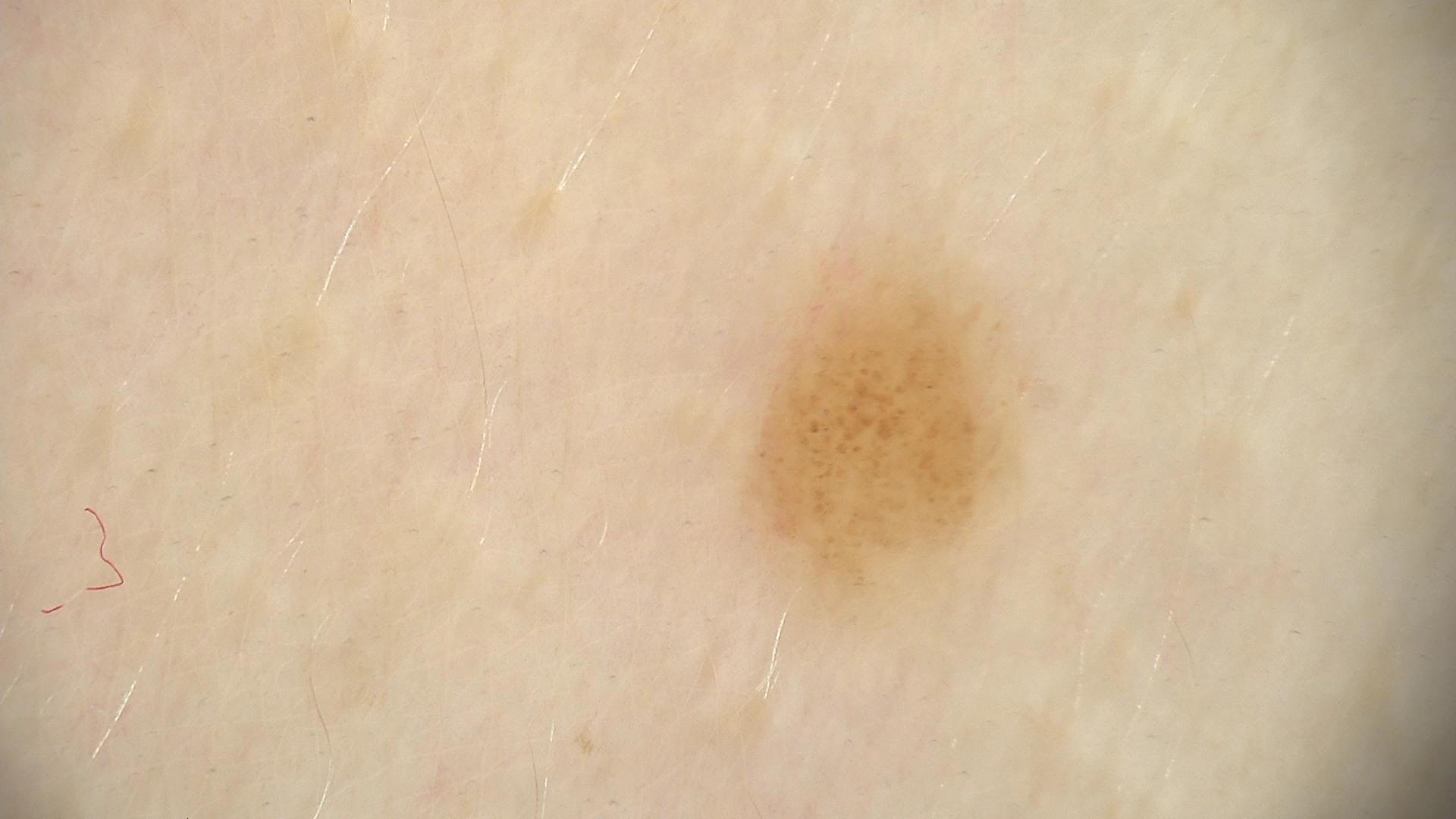The diagnostic label was a banal lesion — a compound nevus.